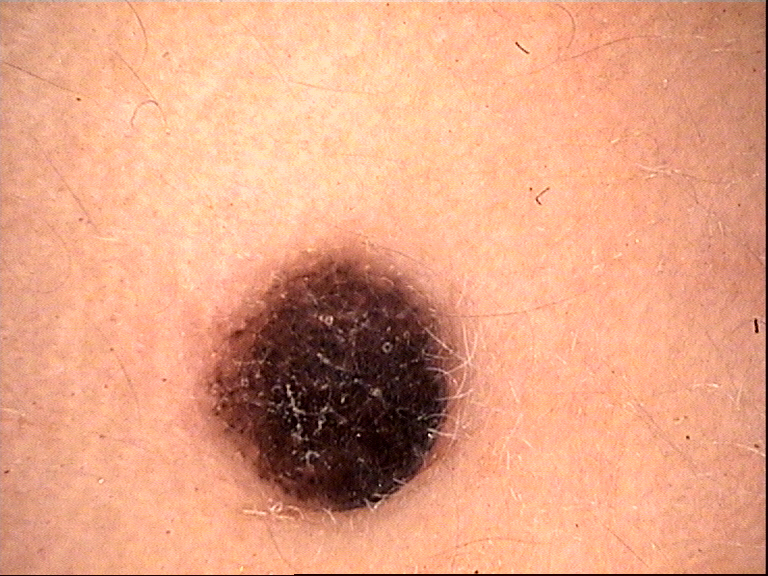Classified as a compound nevus.